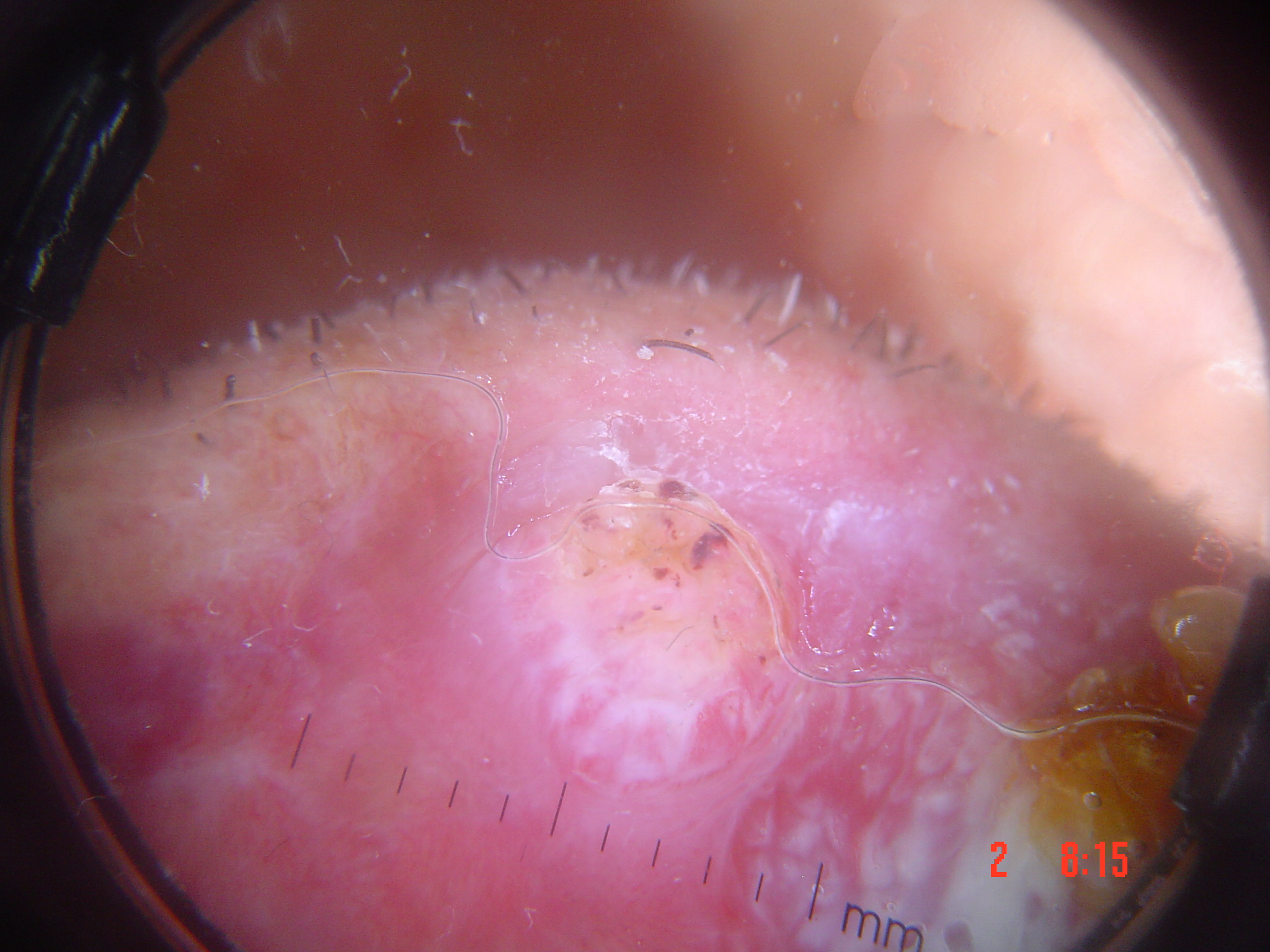Conclusion: The biopsy diagnosis was a squamous cell carcinoma.